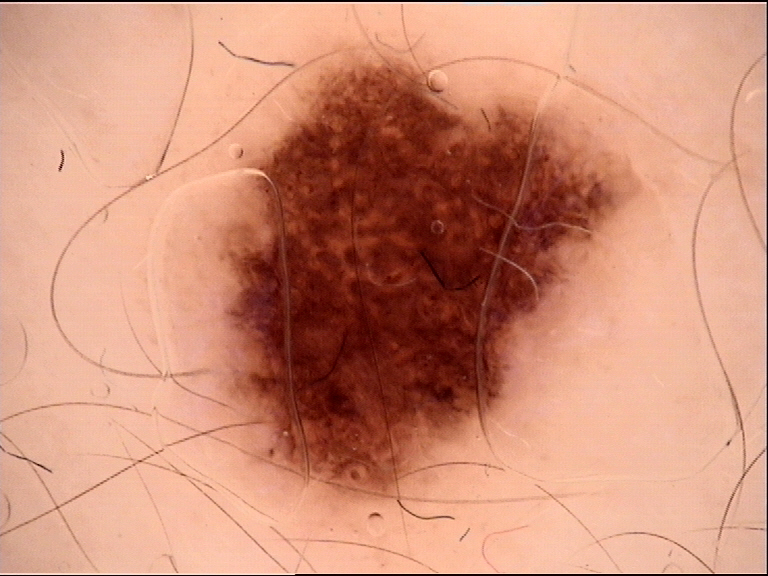Diagnosed as a dysplastic junctional nevus.